A clinical photograph of a skin lesion. A female subject age 64. The patient describes having a moderate number of moles. The patient reports a personal history of cancer and a family history of skin cancer: 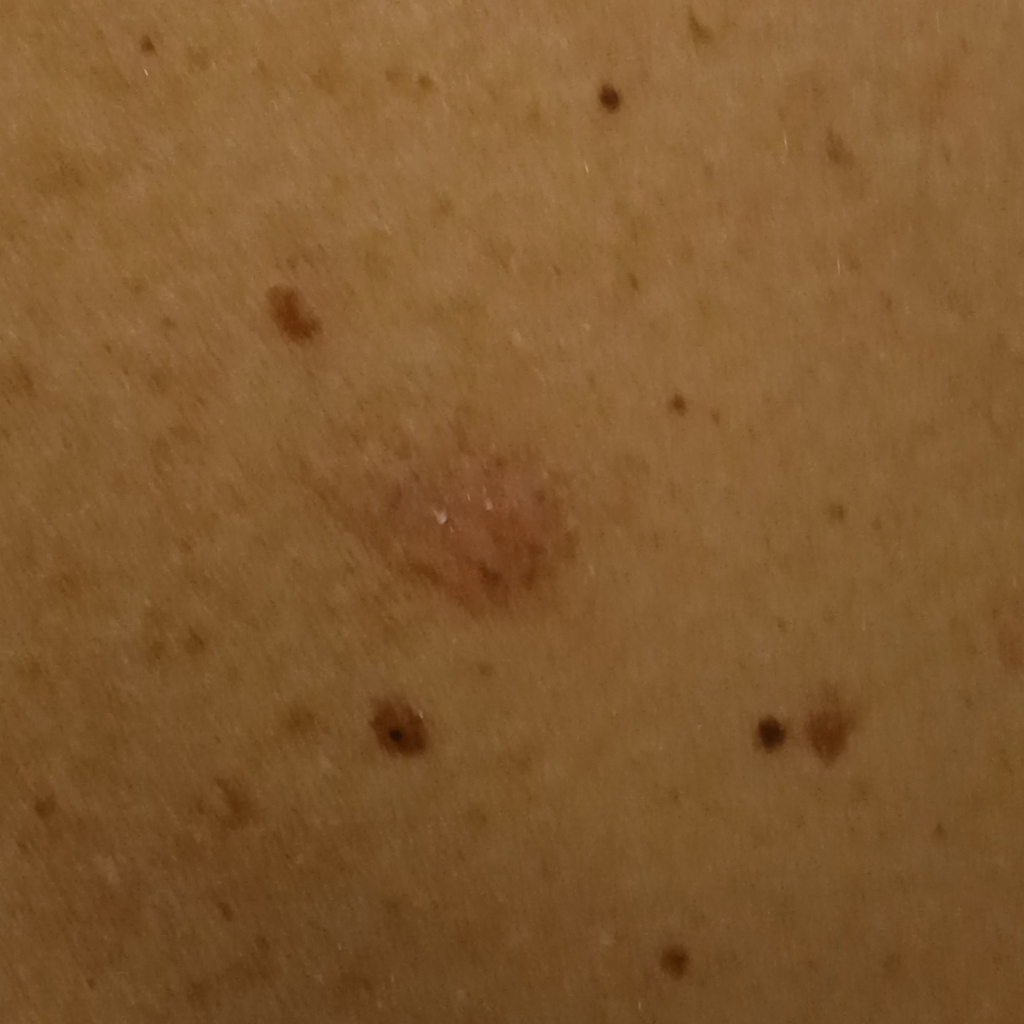location — the back; size — 9.8 mm; diagnosis — basal cell carcinoma (biopsy-proven).